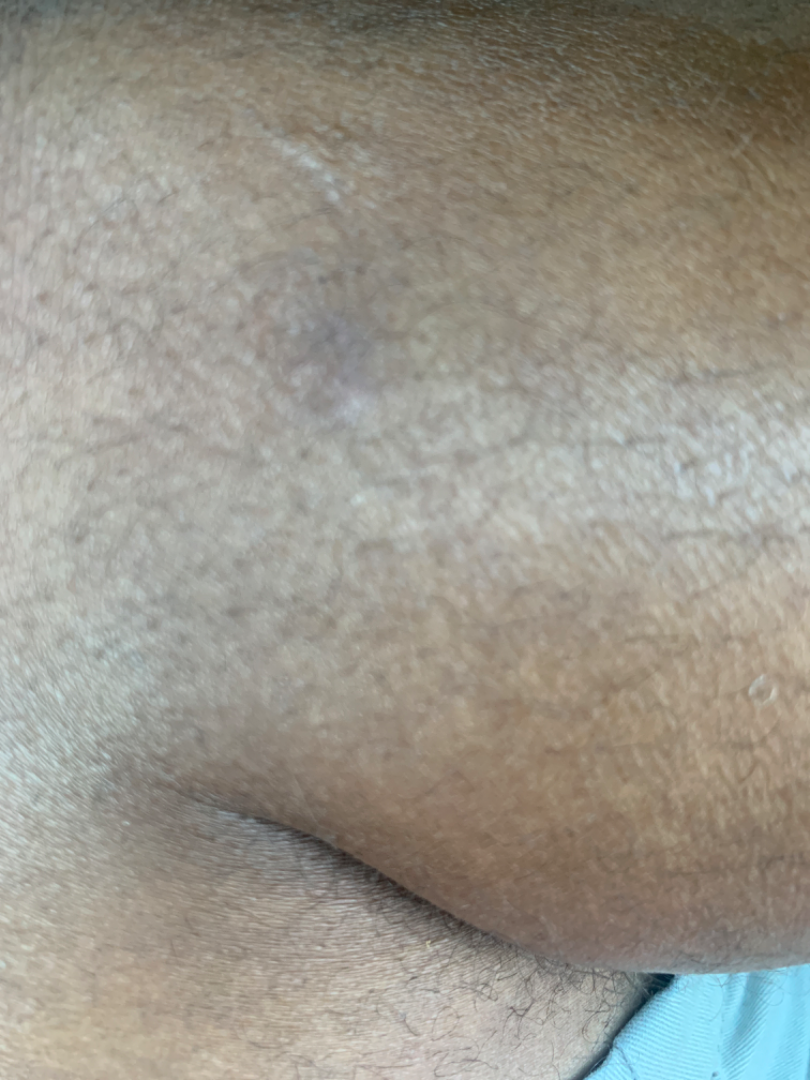assessment — could not be assessed; view — at an angle; skin tone — non-clinician graders estimated Monk skin tone scale 3 or 6; reported symptoms — none reported; location — leg; lesion texture — fluid-filled and rough or flaky.